A male subject roughly 70 years of age. This is a dermoscopic photograph of a skin lesion:
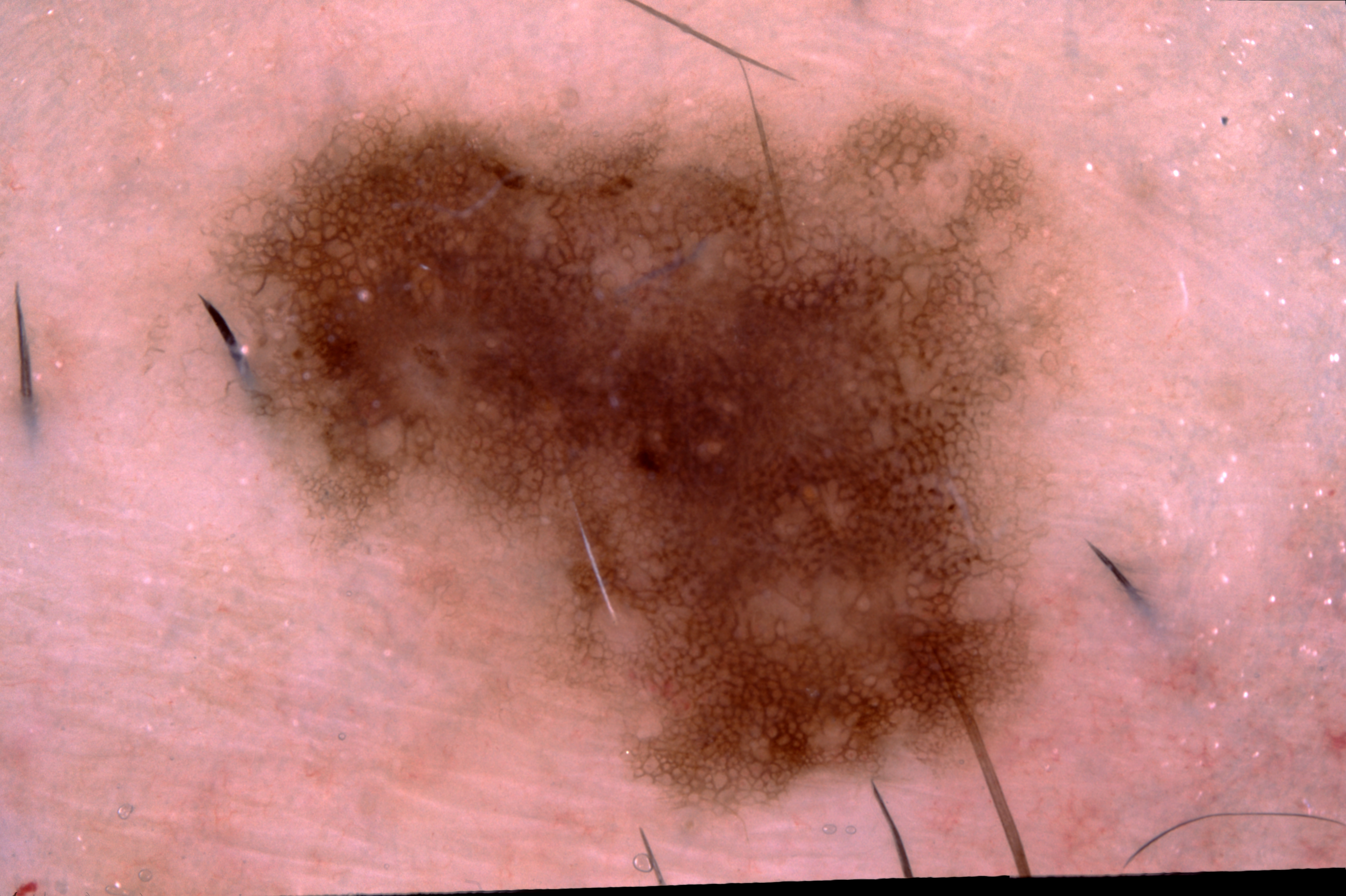dermoscopic_features:
  present:
    - pigment network
  absent:
    - streaks
    - milia-like cysts
    - negative network
lesion_location:
  bbox_xyxy:
    - 133
    - 57
    - 1125
    - 824
lesion_extent: large
diagnosis:
  name: melanocytic nevus
  malignancy: benign
  lineage: melanocytic
  provenance: clinical